The lesion involves the leg. This is a close-up image. Female subject, age 60–69: 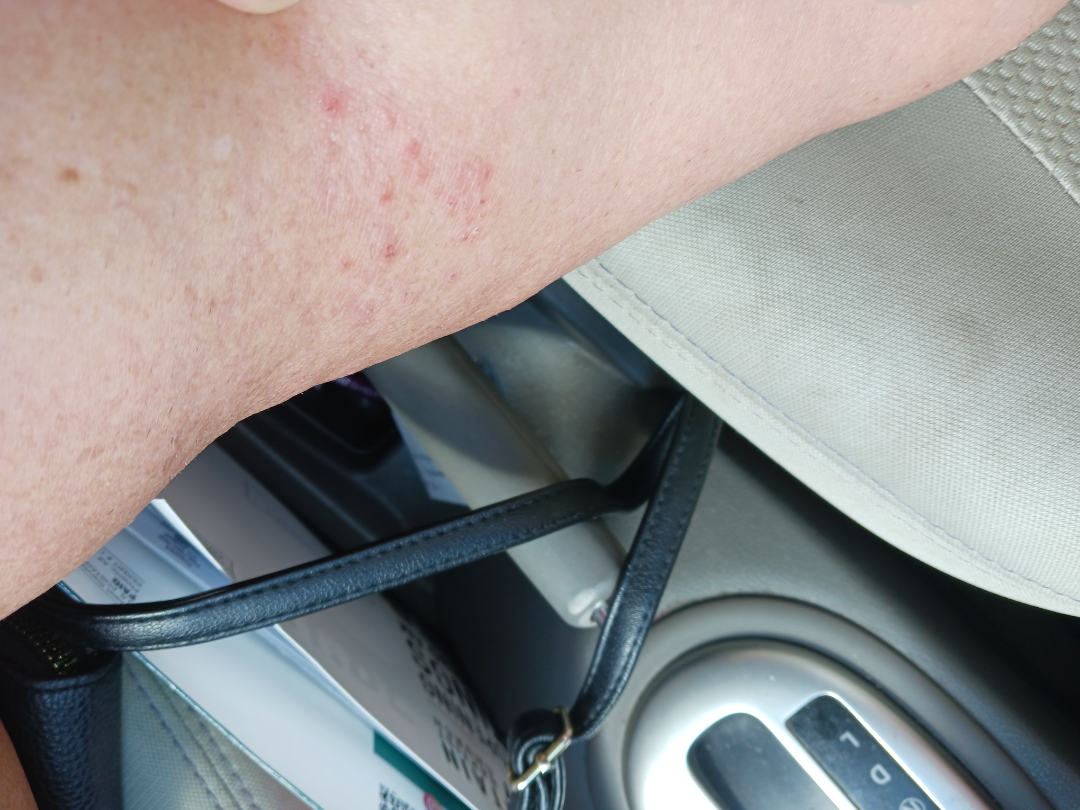On remote dermatologist review: Eczema (weight 1.00).